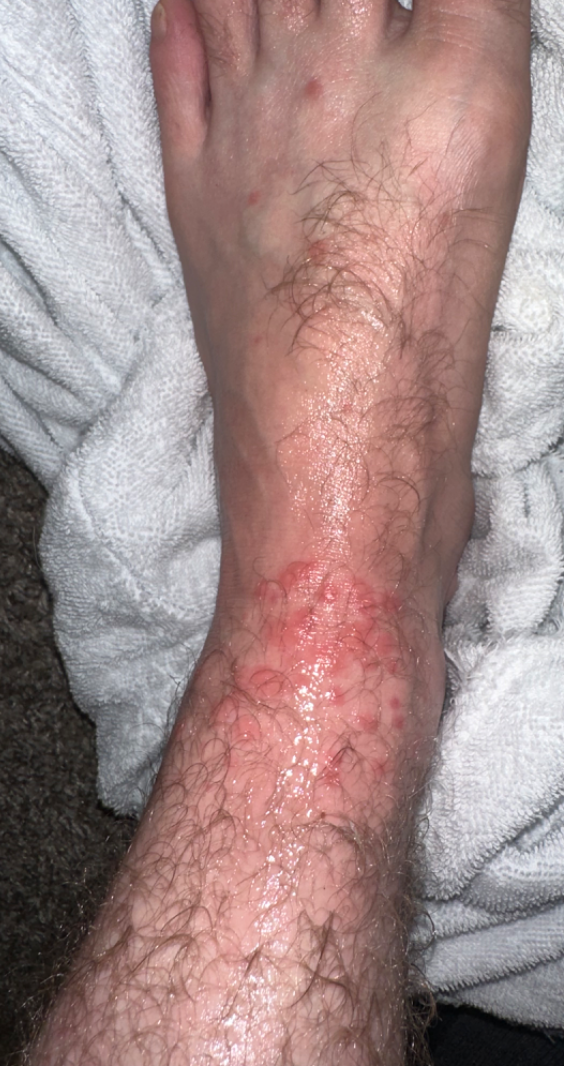The reviewer was unable to grade this case for skin condition. The affected area is the top or side of the foot and leg. This is a close-up image.